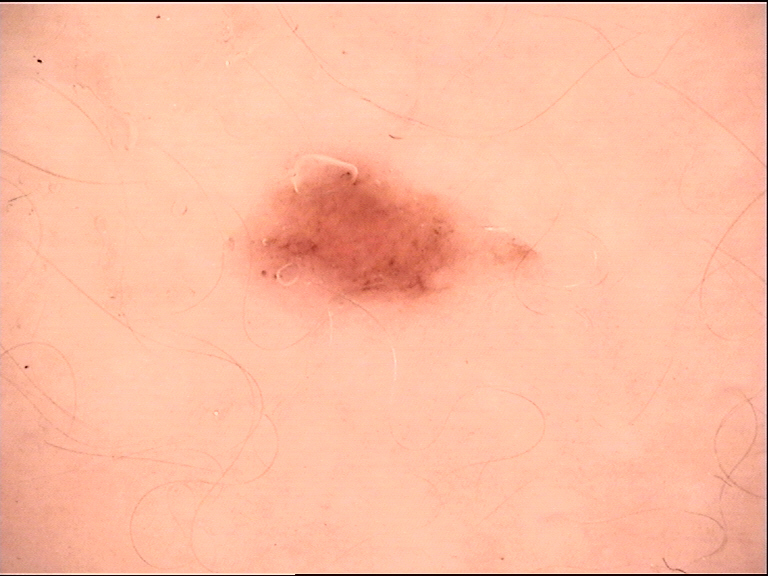Labeled as a dysplastic junctional nevus.